A dermoscopy image of a single skin lesion · a female subject roughly 65 years of age — 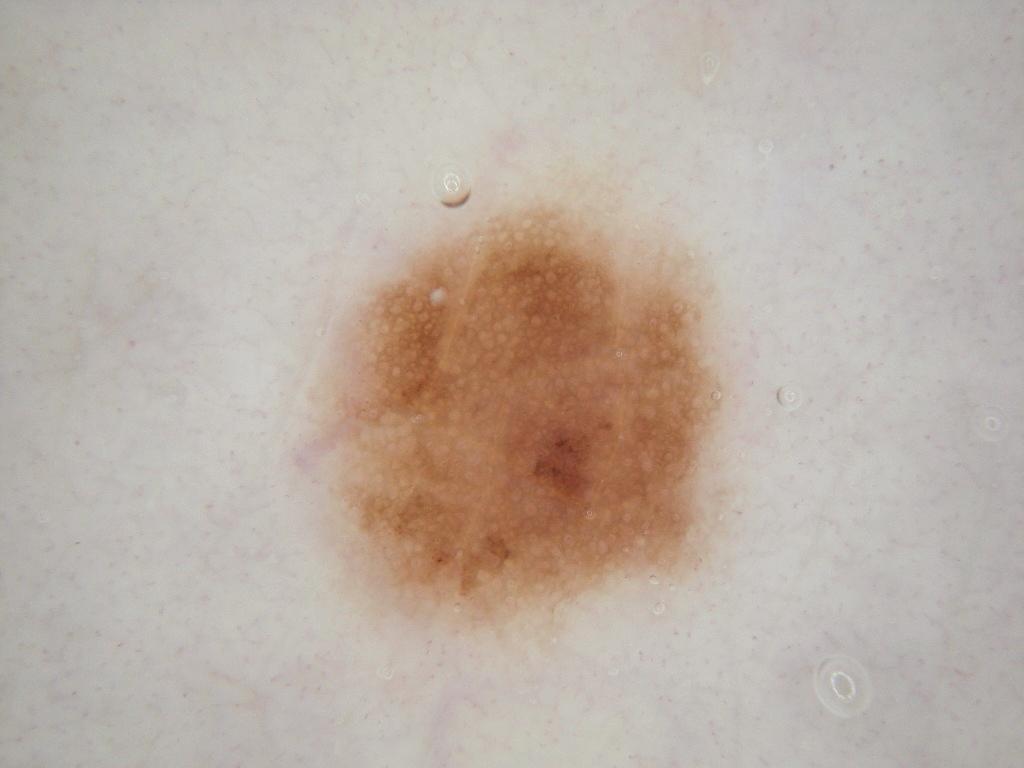Case summary: With coordinates (x1, y1, x2, y2), the lesion is located at 309/182/728/647. The lesion occupies roughly 19% of the field. Dermoscopic examination shows pigment network. Assessment: The clinical diagnosis was a melanocytic nevus, a benign lesion.